Located on the arm · the photograph is a close-up of the affected area — 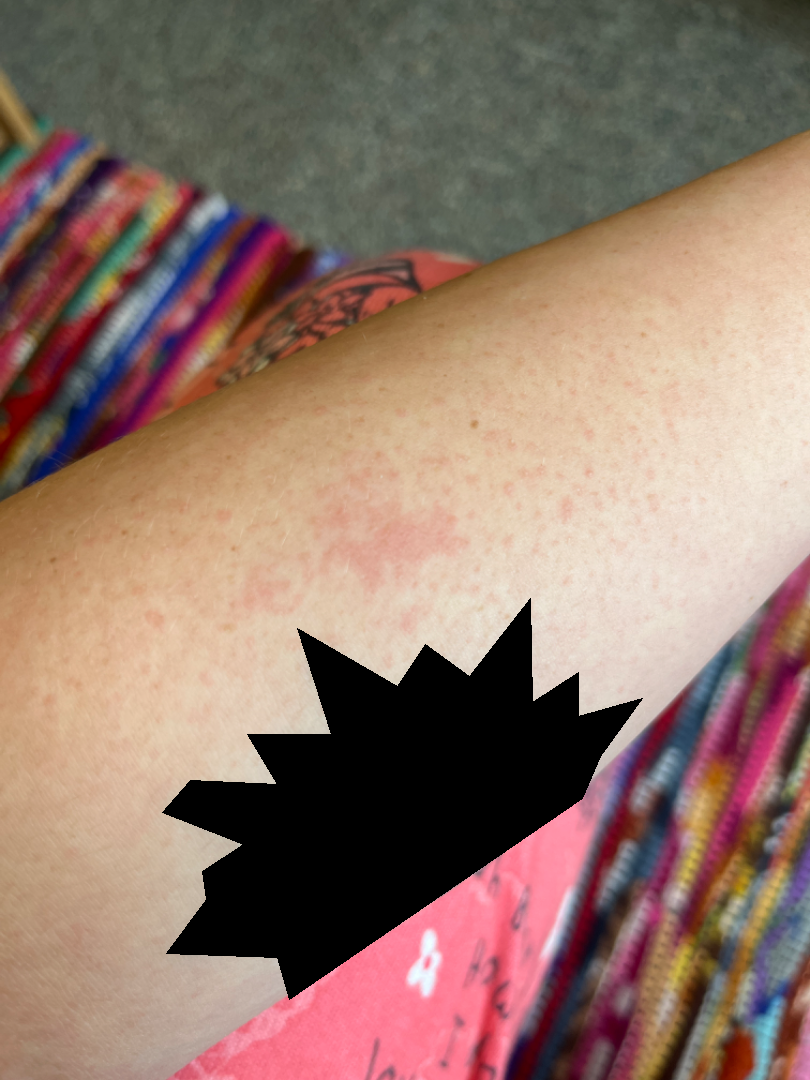Q: What was the assessment?
A: unable to determine